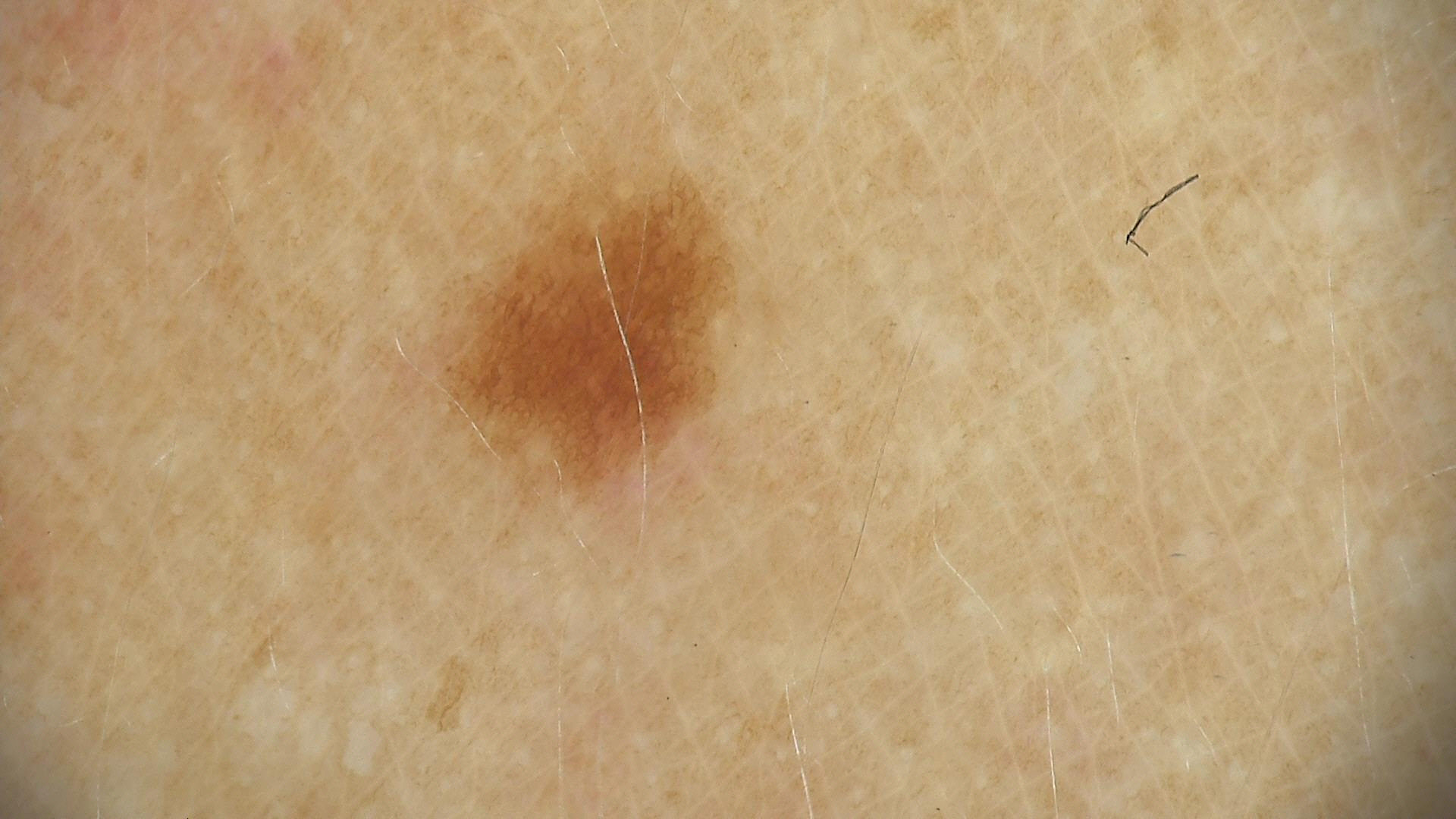Case:
A dermatoscopic image of a skin lesion.
Impression:
Diagnosed as a dysplastic junctional nevus.